A male subject age 79; acquired for a research image collection, with no referral diagnosis.
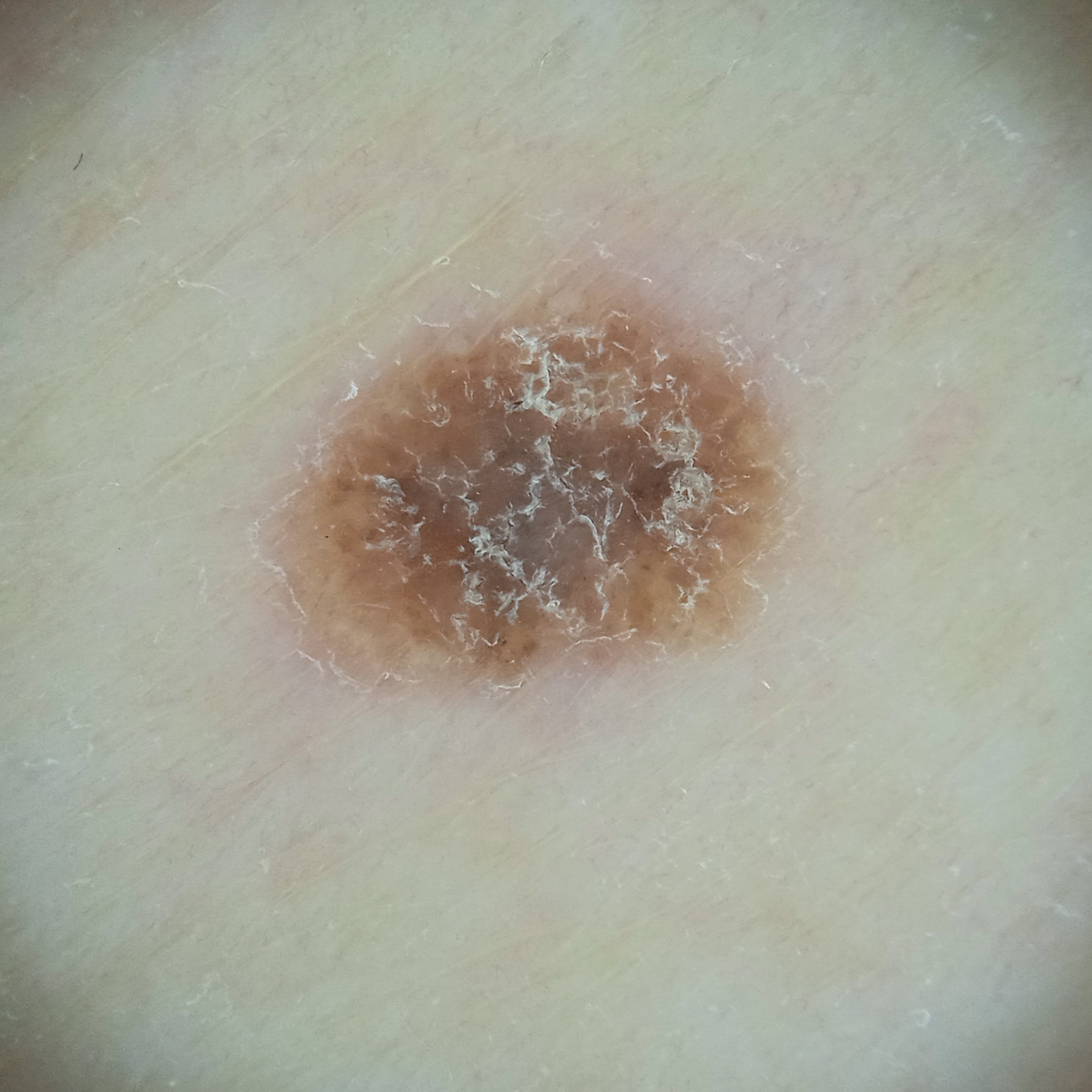The consensus diagnosis for this lesion was a seborrheic keratosis.